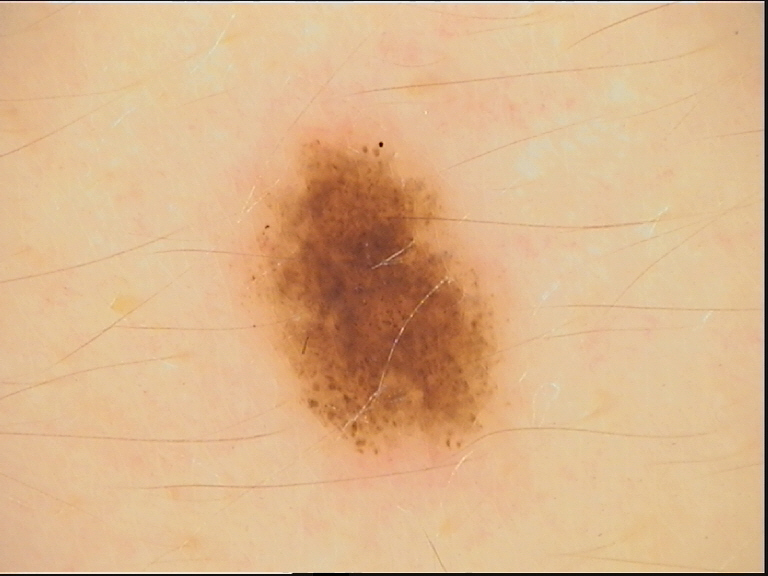The diagnostic label was a benign lesion — a dysplastic junctional nevus.